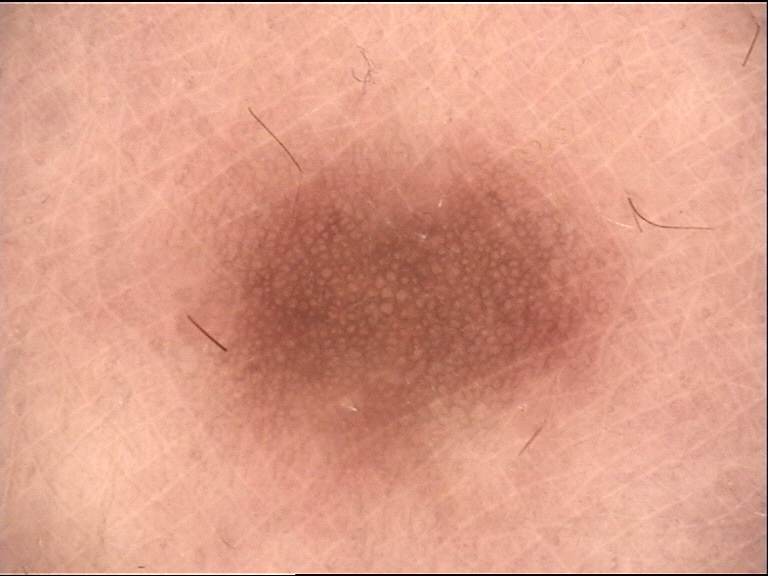A dermoscopic photograph of a skin lesion.
This is a fibro-histiocytic lesion.
Consistent with a dermatofibroma.